The lesion is described as rough or flaky and flat · skin tone: FST III · reported duration is one to three months · this is a close-up image · the patient is 30–39, female · located on the arm, leg, back of the hand and top or side of the foot · symptoms reported: bothersome appearance and itching · associated systemic symptoms include fatigue:
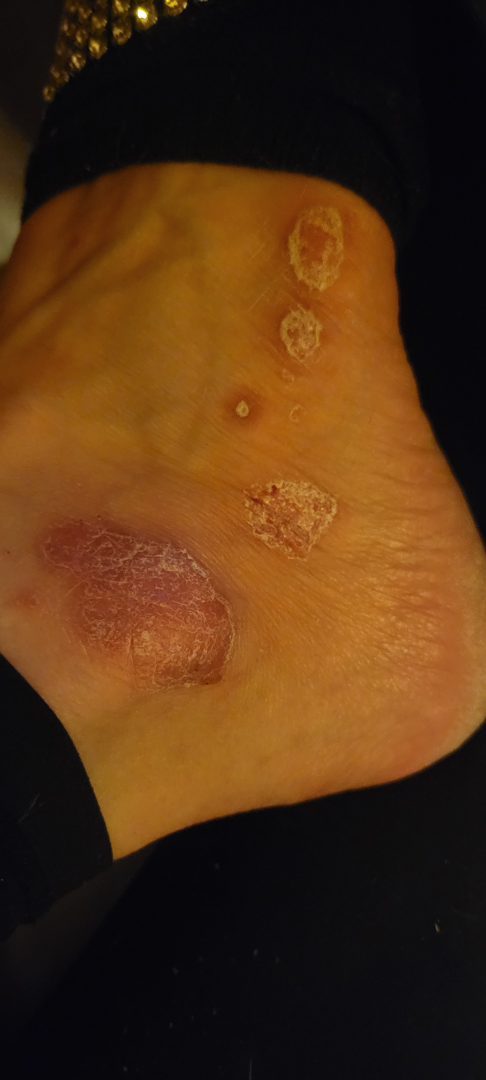Q: What is the dermatologist's impression?
A: the leading consideration is Psoriasis; also consider Tinea; possibly Eczema